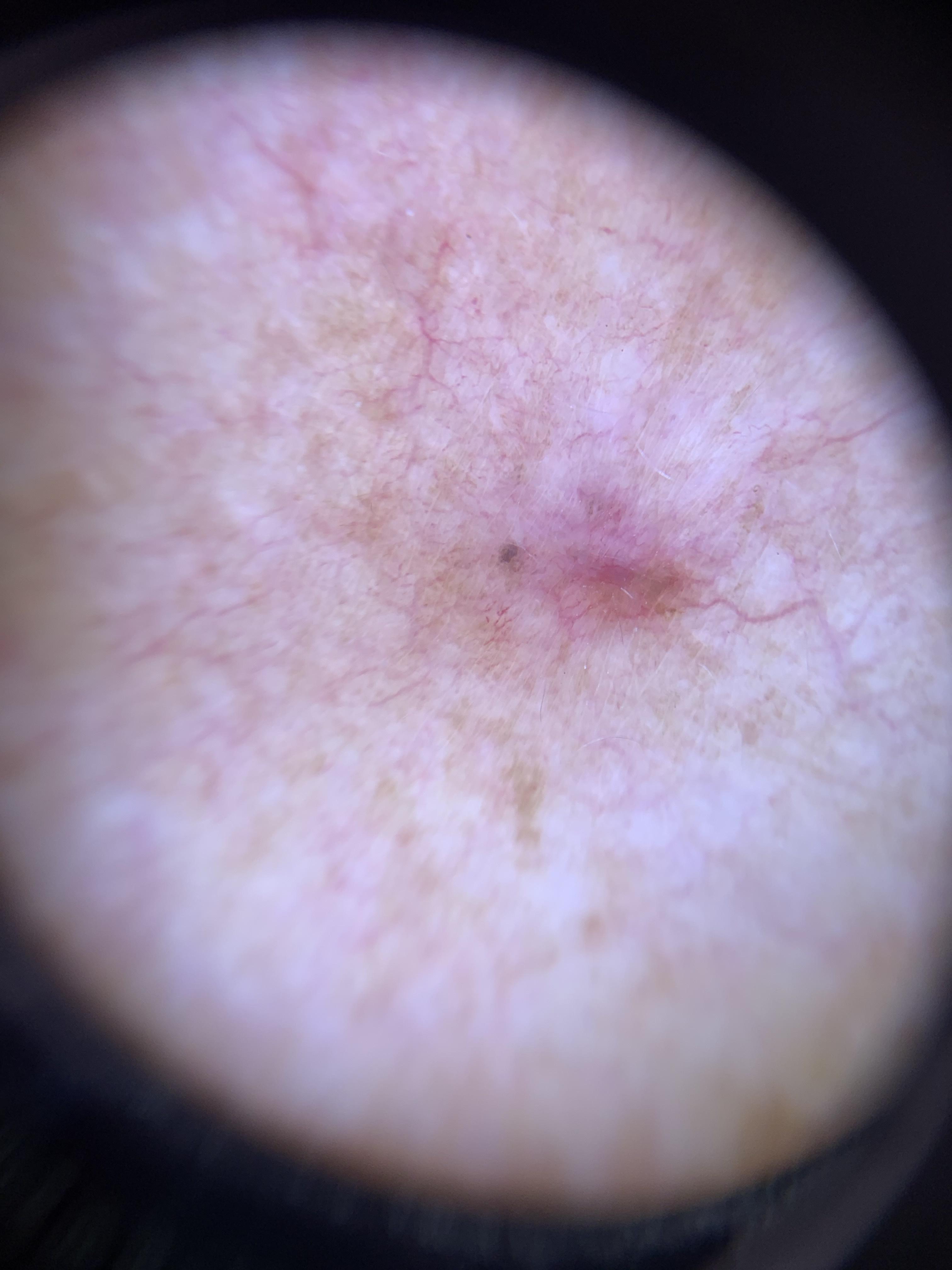A skin lesion imaged with contact-polarized dermoscopy.
A female patient roughly 85 years of age or older.
Recorded as Fitzpatrick II.
The lesion is located on the trunk.
Biopsy-confirmed as a basal cell carcinoma.